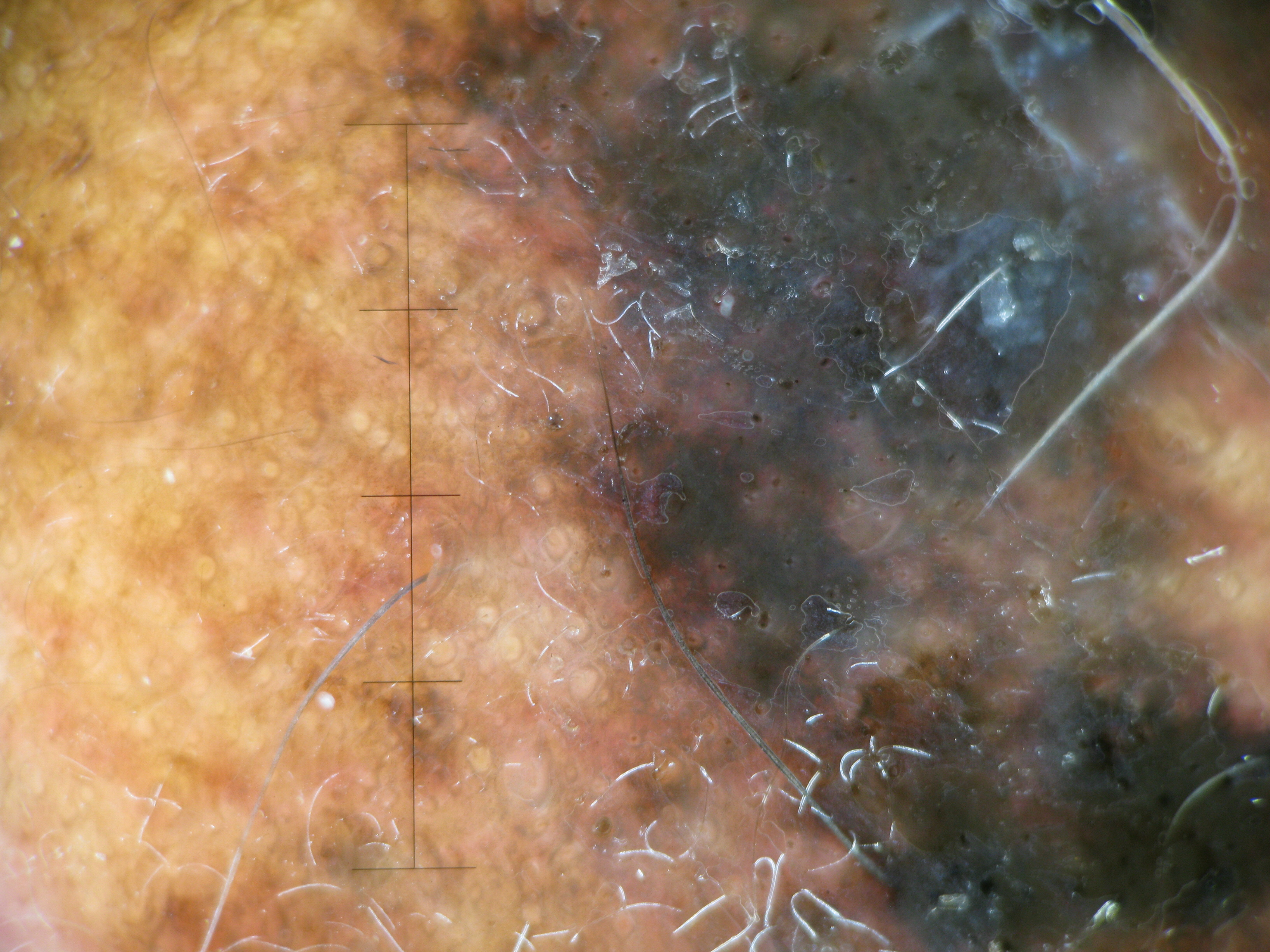A dermoscopic close-up of a skin lesion. Histopathology confirmed a malignant lesion — a lentigo maligna melanoma.